Located on the leg. This is a close-up image. The subject is female:
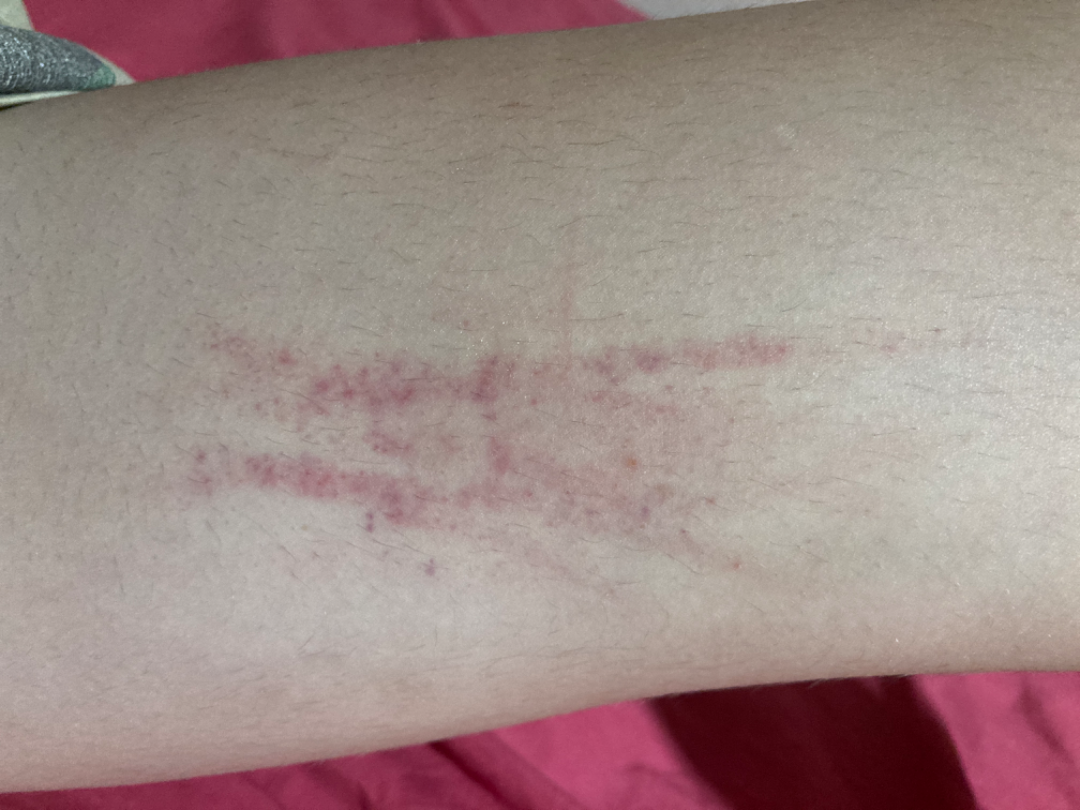Case summary:
• patient describes the issue as — a rash
• history — about one day
• differential — ecchymoses (favored); Superficial wound of body region (possible); Purpura (less likely)